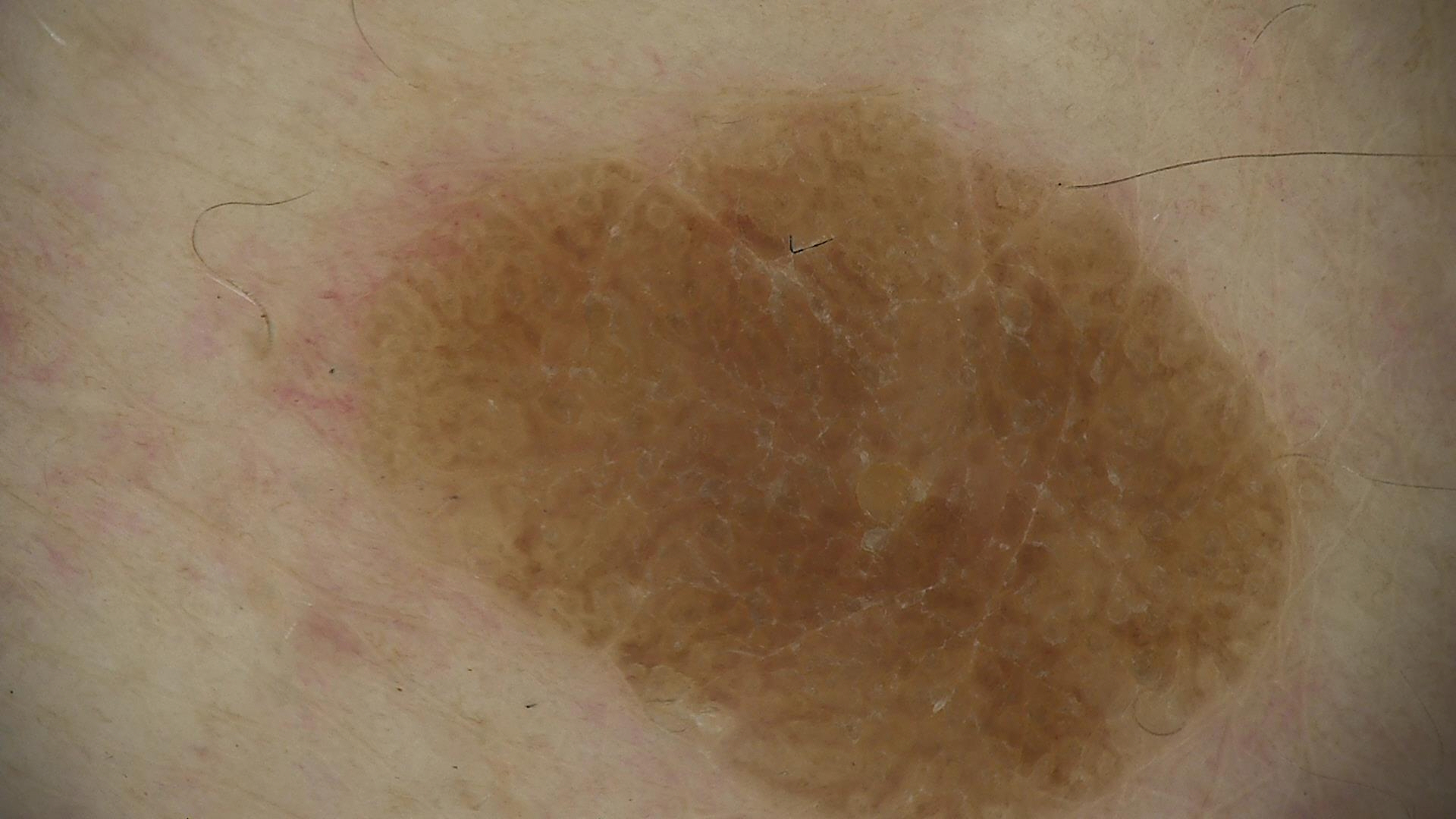Impression:
Diagnosed as a keratinocytic lesion — a seborrheic keratosis.